The leg is involved. Female contributor, age 18–29. This is a close-up image: 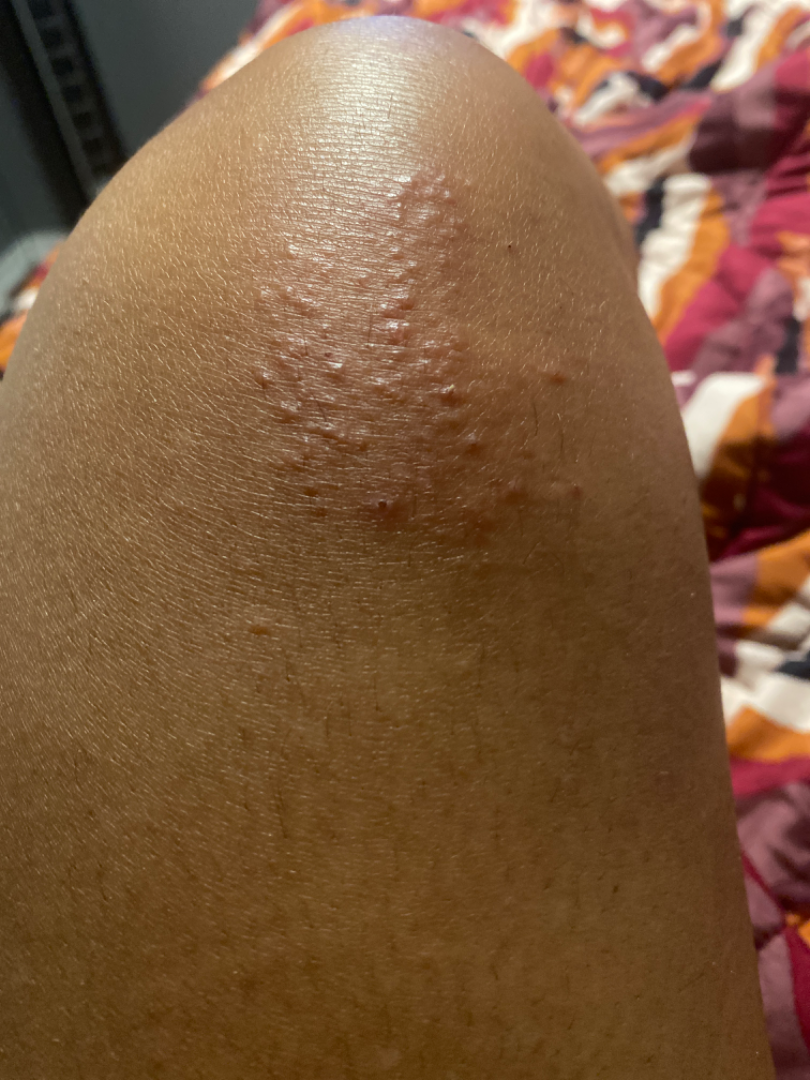differential:
  leading:
    - Lichen spinulosus
  considered:
    - Keratosis pilaris
  unlikely:
    - Lichen nitidus